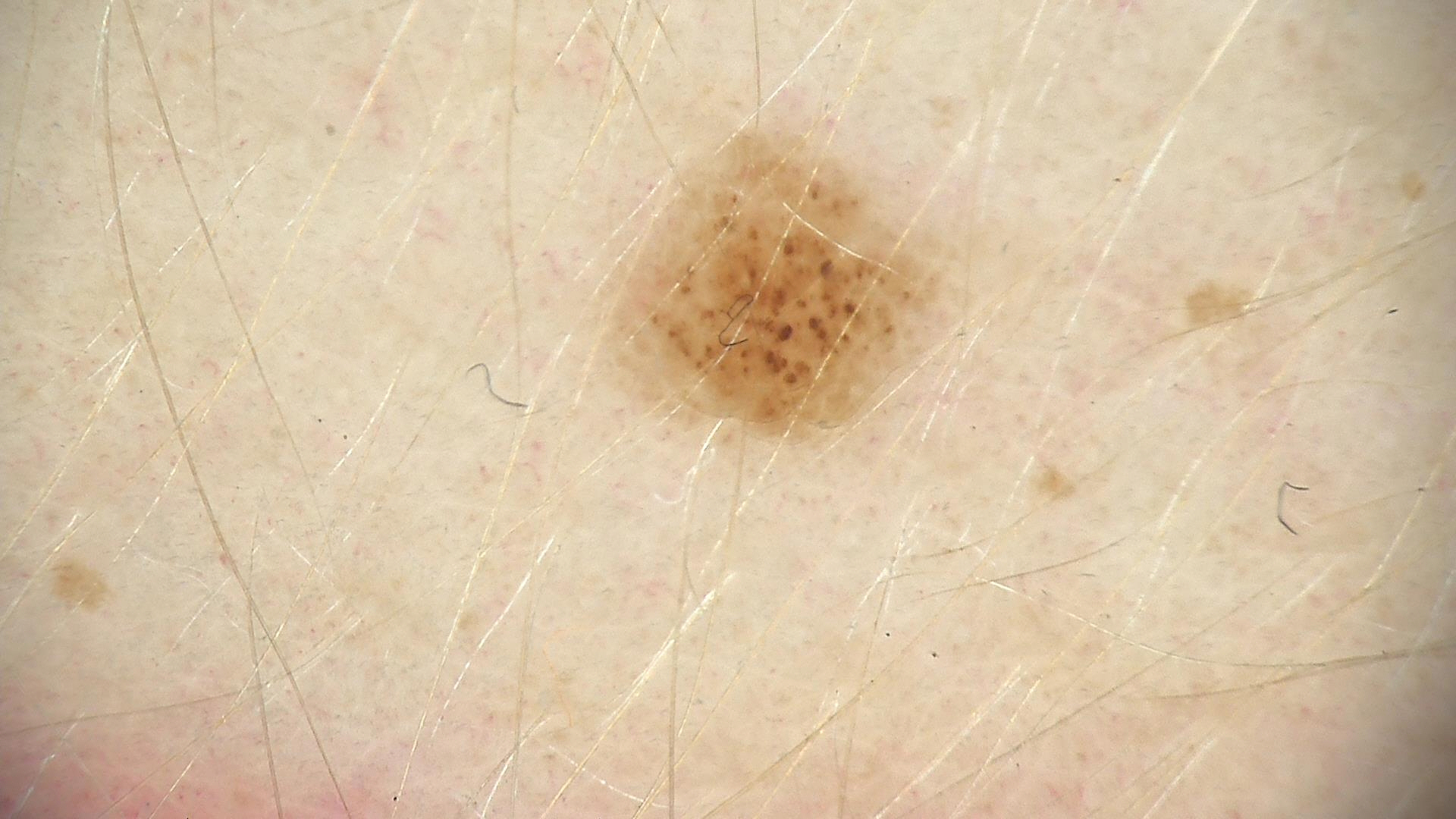Dermoscopy of a skin lesion. The diagnosis was a dysplastic junctional nevus.